By history, prior malignancy (patient or family) · skin type II · a clinical photo of a skin lesion taken with a smartphone · a male patient 90 years of age.
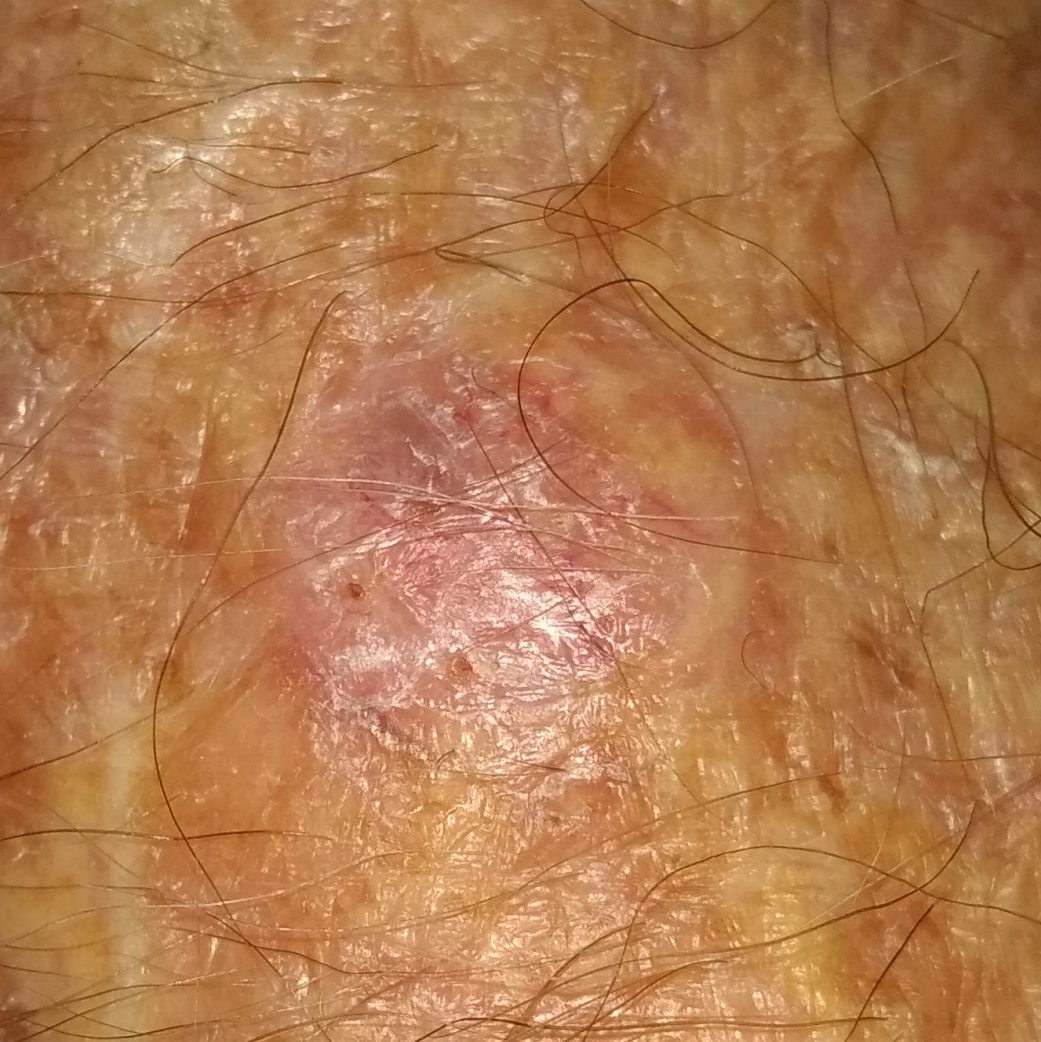Findings: The lesion is located on the face. Conclusion: Biopsy-confirmed as a basal cell carcinoma.